A dermatoscopic image of a skin lesion: 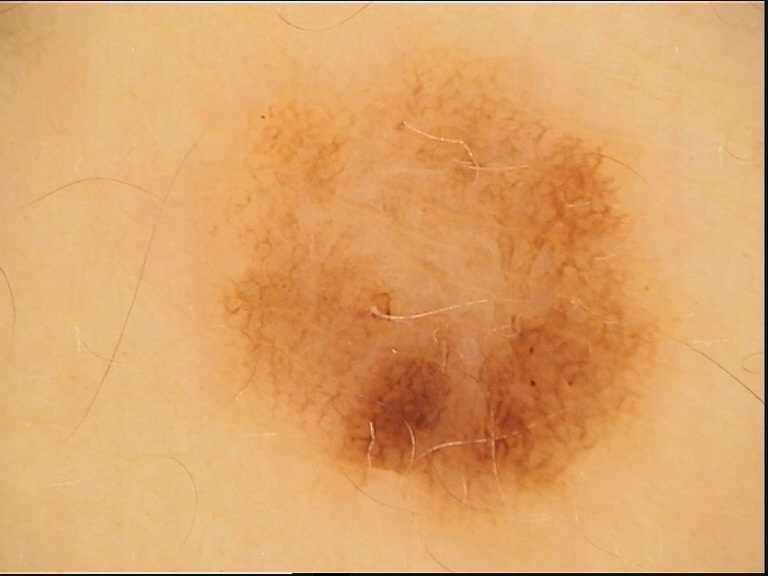Diagnosed as a benign lesion — a dysplastic junctional nevus.